A skin lesion imaged with a dermatoscope · per the chart, a first-degree relative with melanoma · FST III · a male subject aged 38 to 42 — 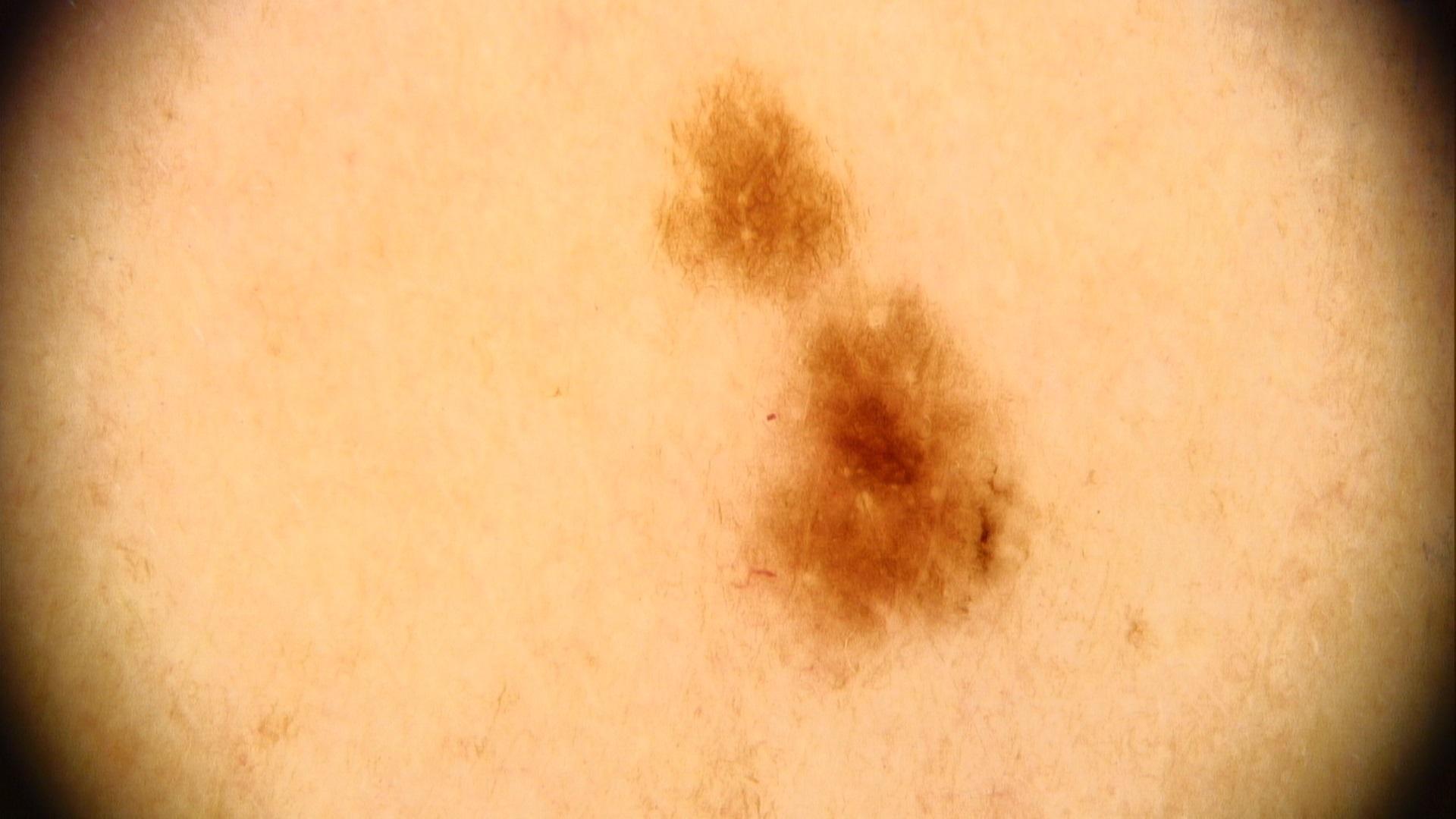• location · the trunk, specifically the posterior trunk
• assessment · Nevus